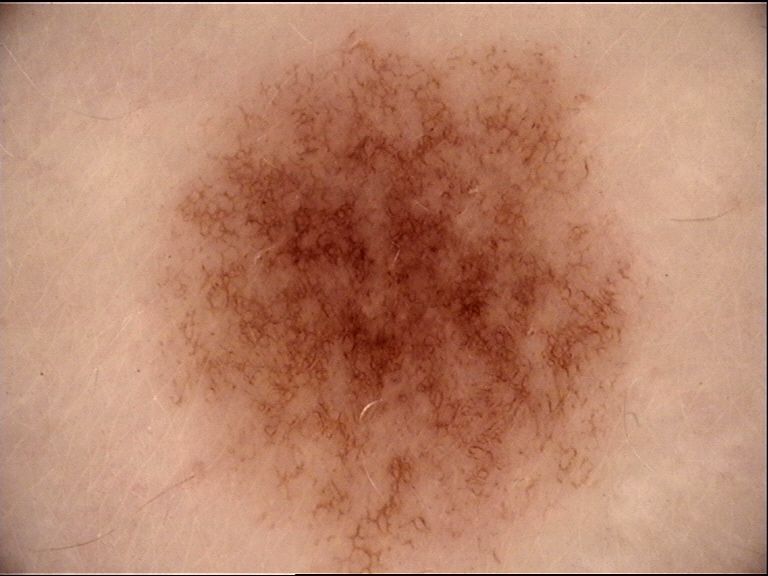Q: What is the imaging modality?
A: dermoscopy
Q: What was the diagnostic impression?
A: dysplastic junctional nevus (expert consensus)